A dermatoscopic image of a skin lesion.
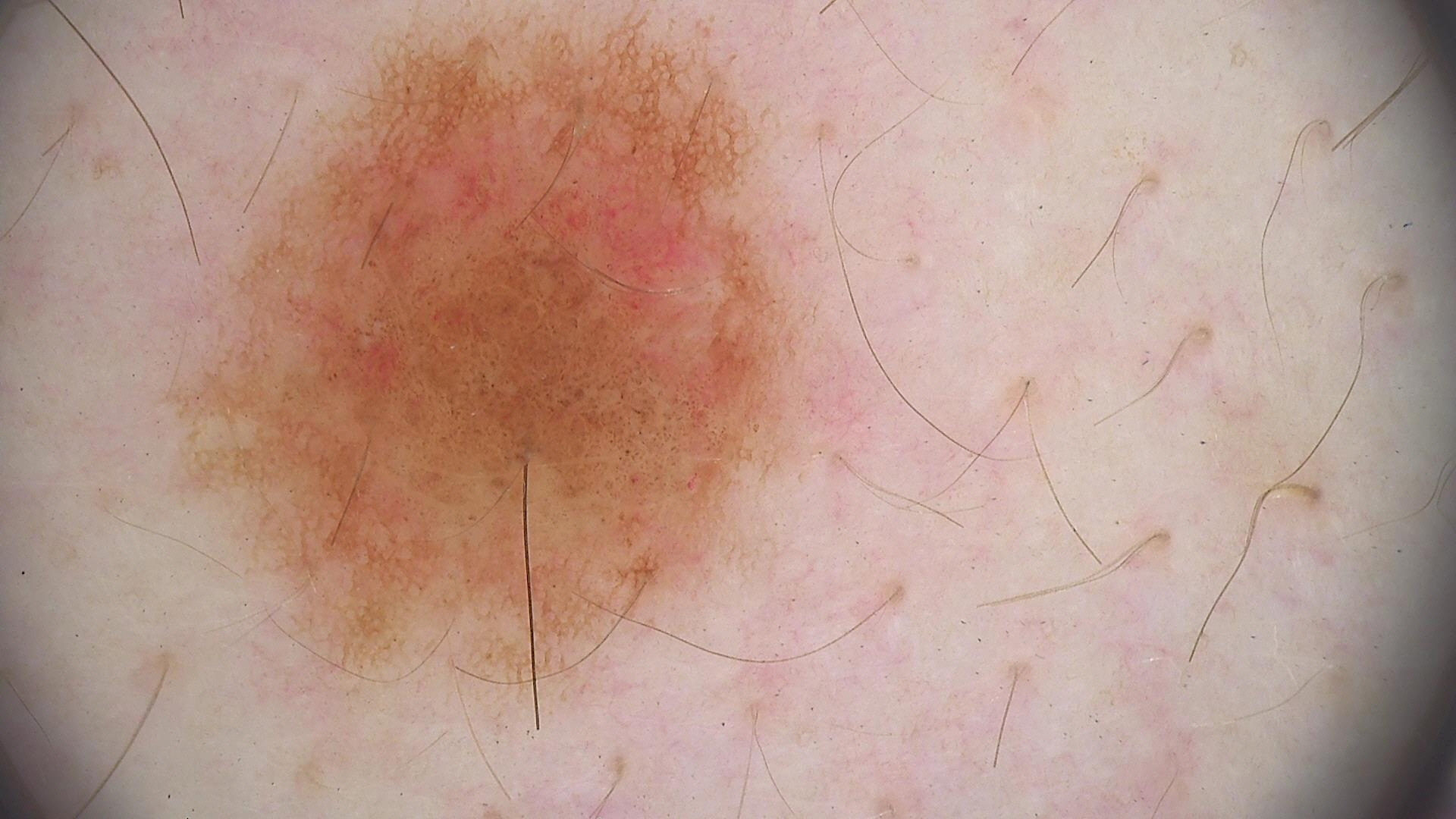The diagnosis was a benign lesion — a dysplastic compound nevus.